A clinical photograph of a skin lesion · by history, prior malignancy (patient or family) and no alcohol use · a female subject 63 years old · the patient was assessed as skin type IV:
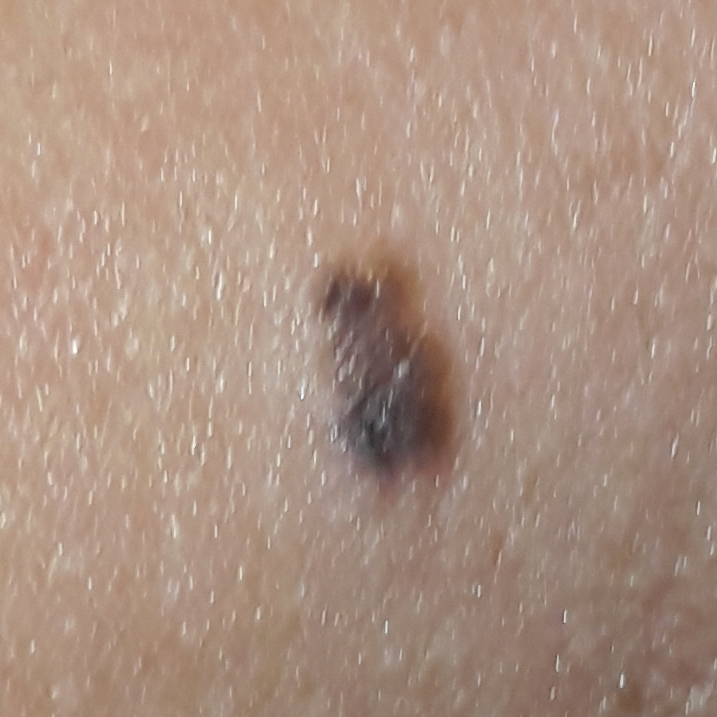Patient and lesion:
The lesion is on the neck. Per patient report, the lesion has grown and has changed.
Diagnosis:
Histopathology confirmed a benign skin lesion — a seborrheic keratosis.